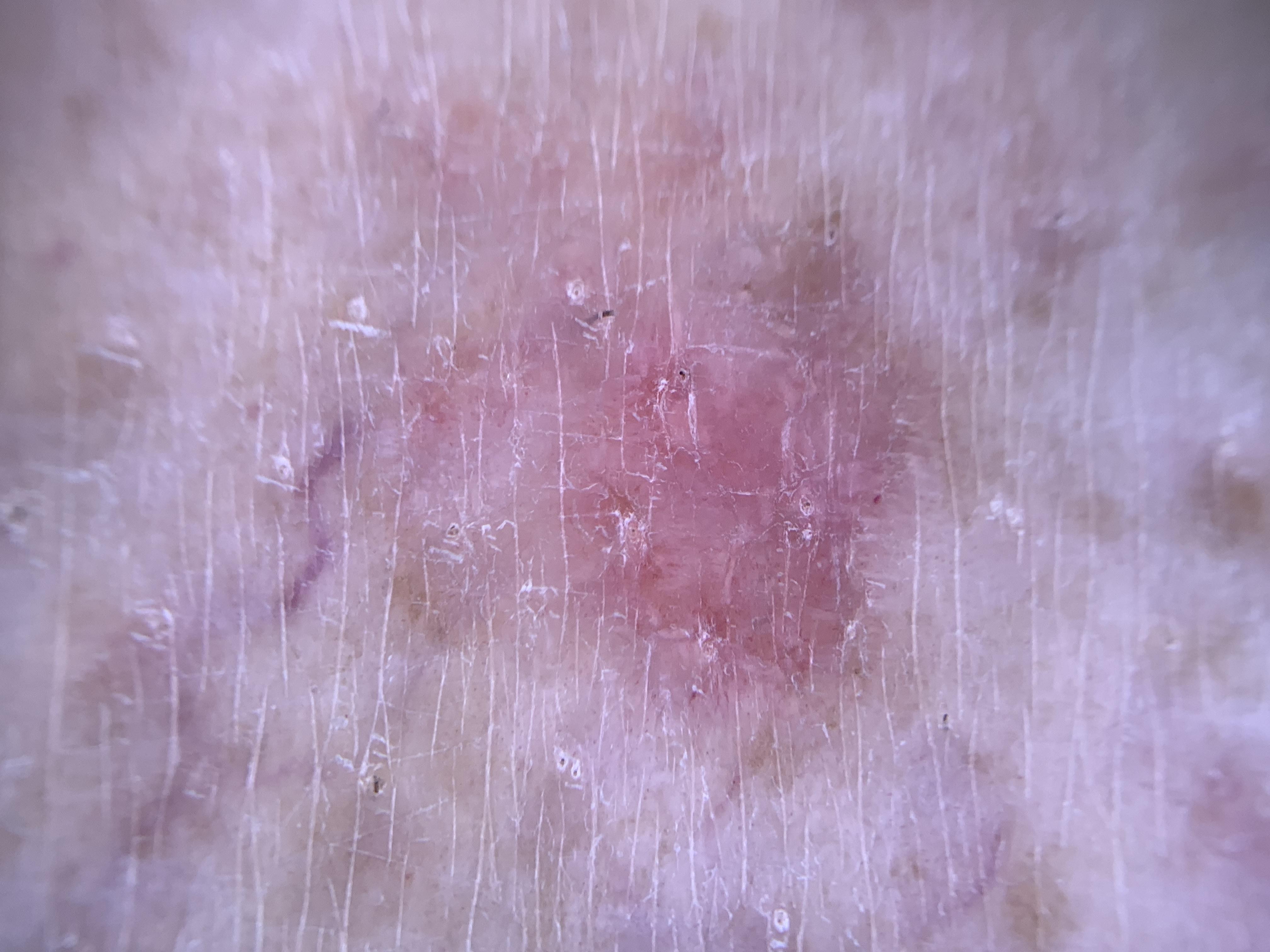image type: dermoscopic image; subject: male, about 75 years old; location: a lower extremity; pathology: Basal cell carcinoma (biopsy-proven).